Close-up view; the affected area is the leg; self-categorized by the patient as a rash; the lesion is described as raised or bumpy; present for less than one week; female contributor, age 60–69; the patient also reports joint pain; the lesion is associated with itching:
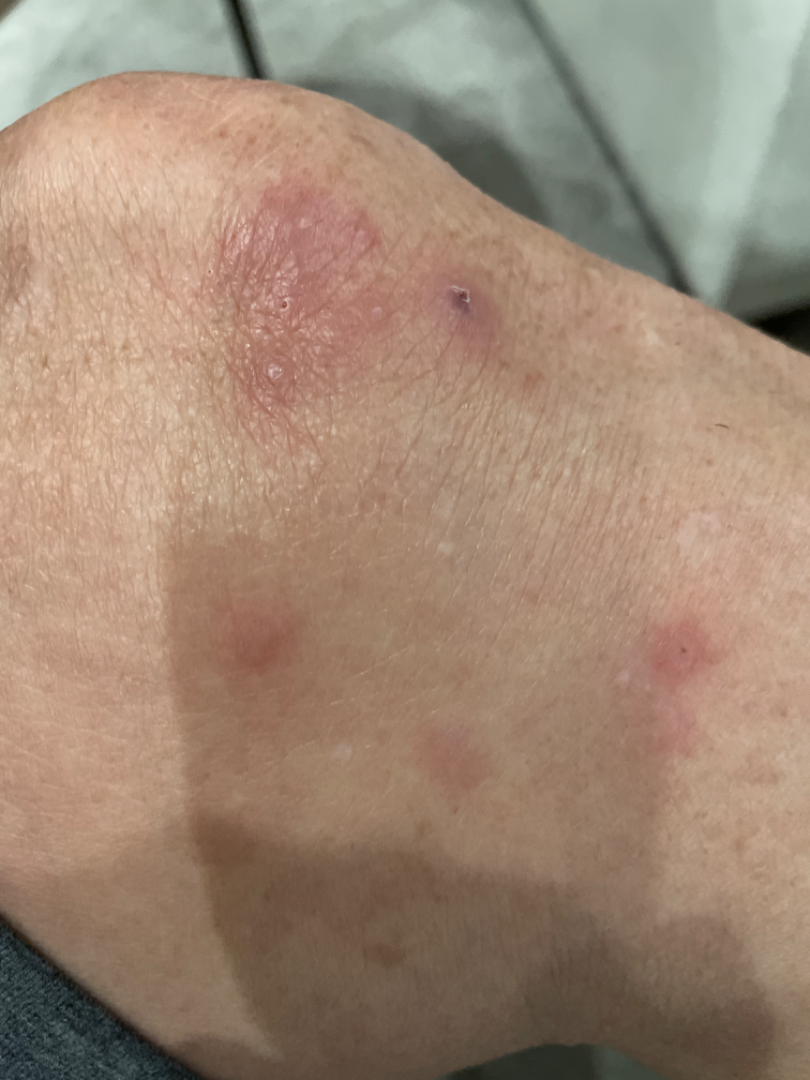assessment: Skin infection (0.41); Folliculitis (0.41); Eczema (0.18).